Dermoscopy of a skin lesion:
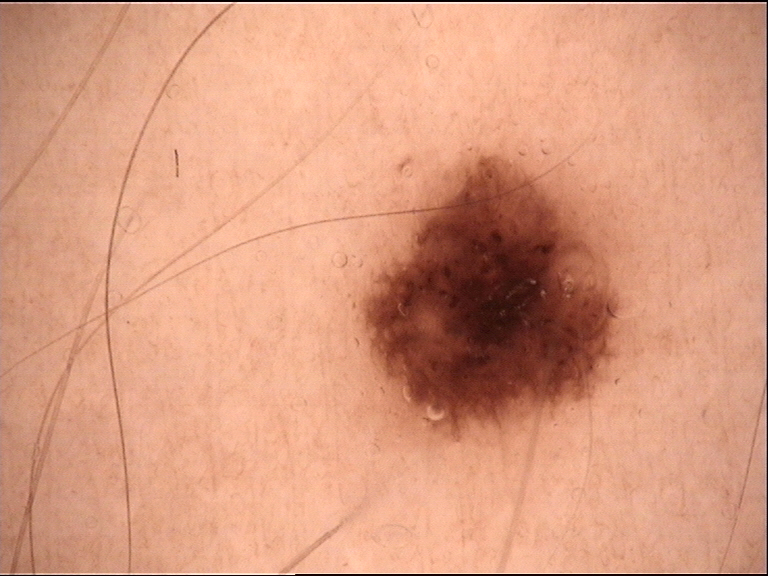diagnosis:
  name: dysplastic junctional nevus
  code: jd
  malignancy: benign
  super_class: melanocytic
  confirmation: expert consensus